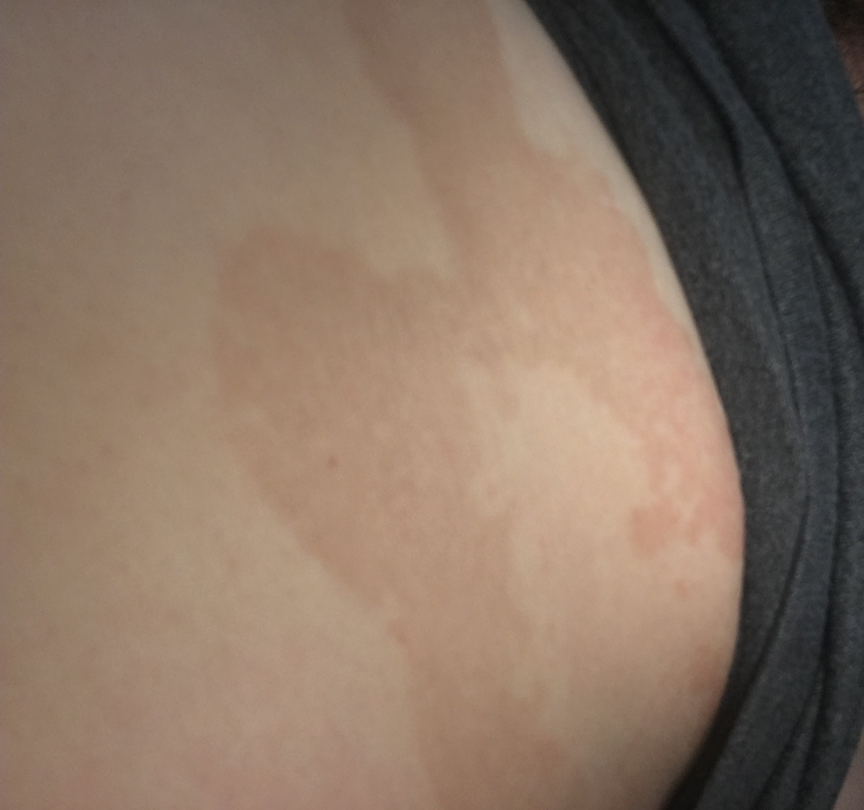Findings:
The reviewing dermatologist was unable to assign a differential diagnosis from the image.
Background:
The patient described the issue as a rash. This image was taken at an angle. No constitutional symptoms were reported. Located on the front of the torso and back of the torso.